This image was taken at an angle. Reported lesion symptoms include enlargement, pain, itching and bothersome appearance. Reported duration is less than one week. Skin tone: non-clinician graders estimated Monk Skin Tone 2. The lesion is described as raised or bumpy. The affected area is the back of the torso. The patient also reports chills — 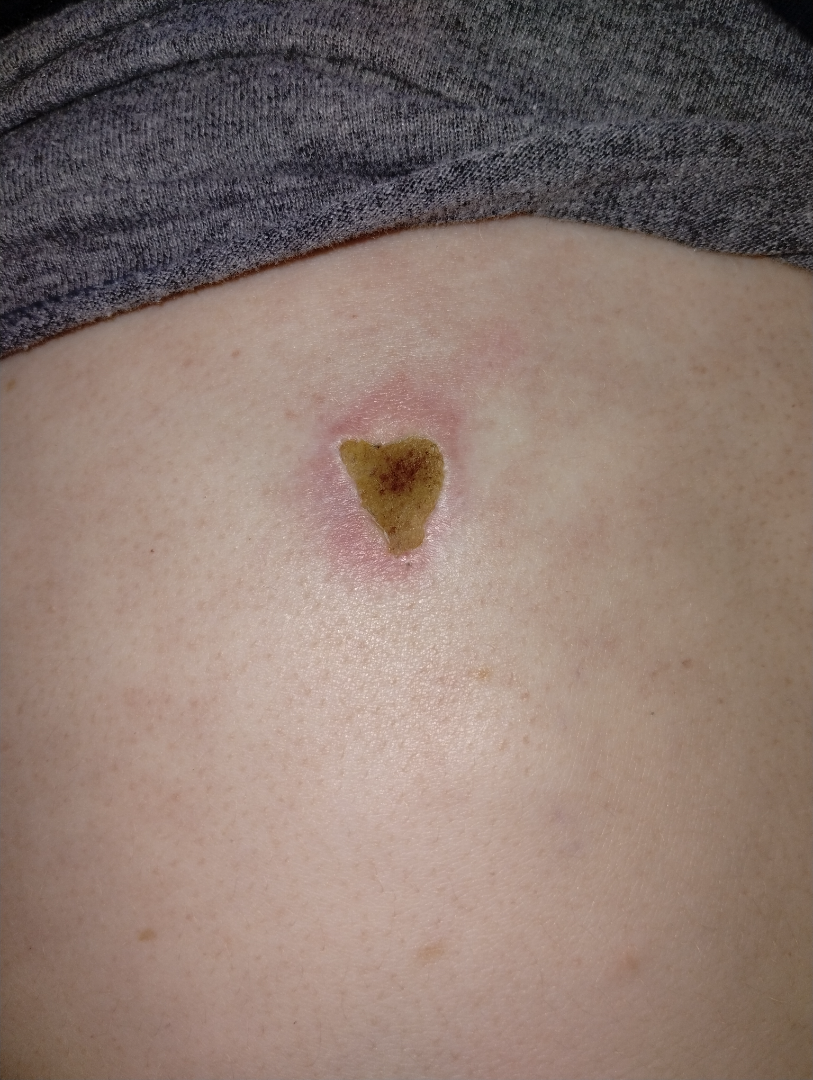The image was not sufficient for the reviewer to characterize the skin condition.